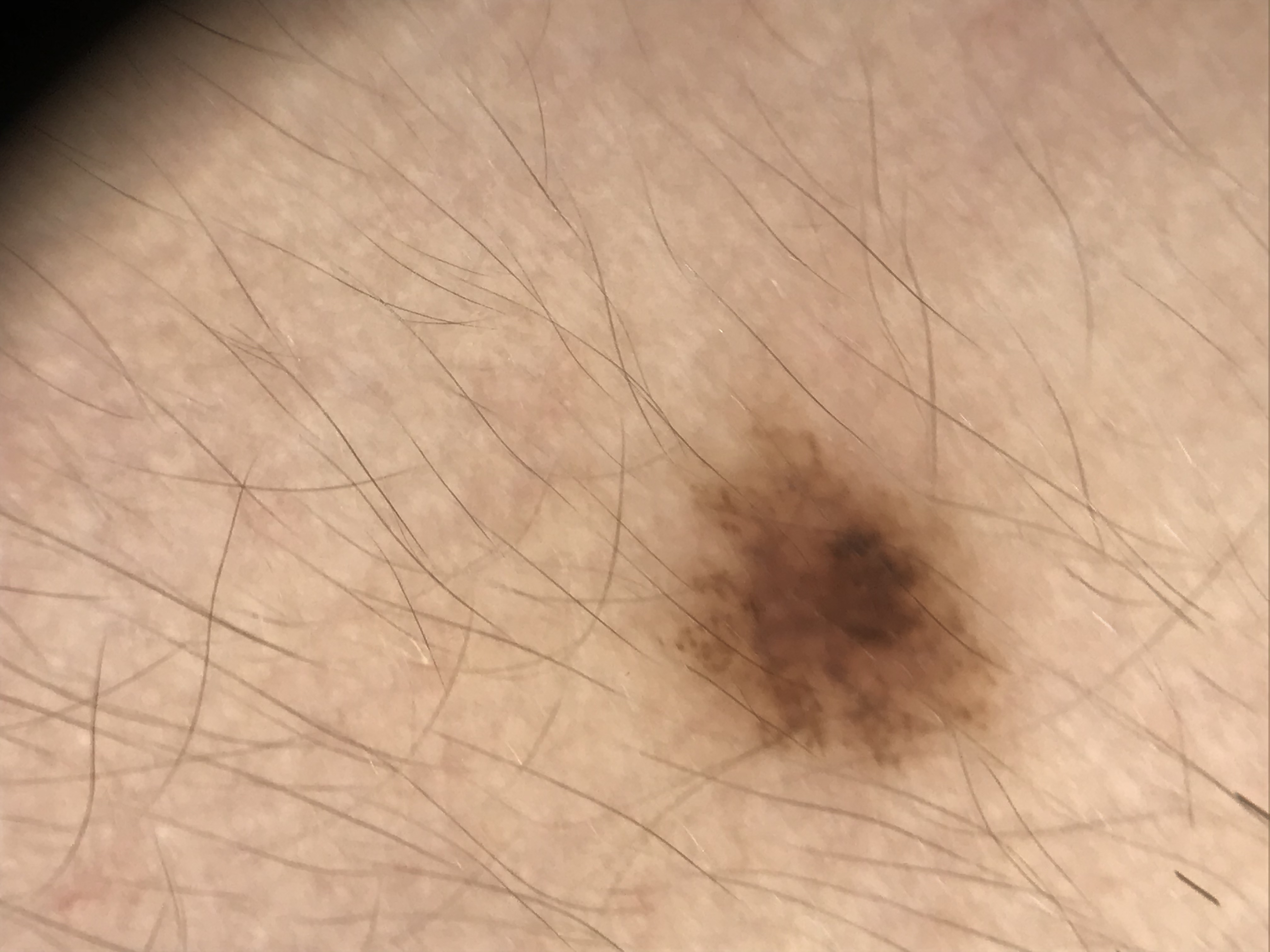image: dermoscopy; label: dysplastic junctional nevus (expert consensus).